A dermoscopic image of a skin lesion. A female patient, aged 28-32:
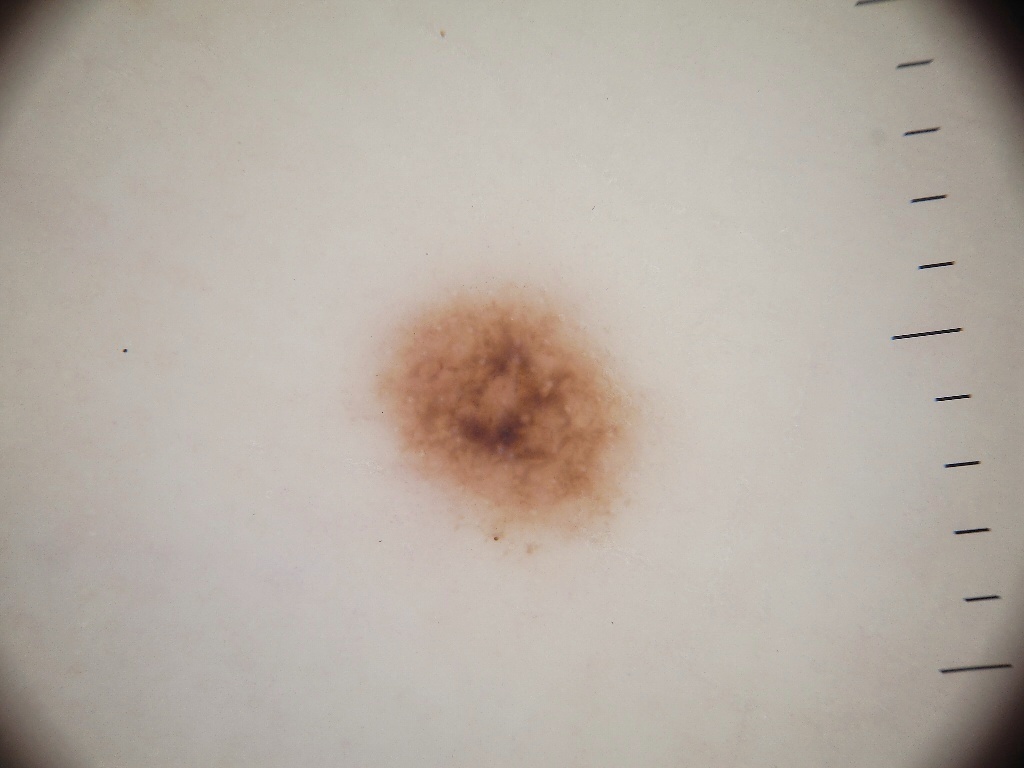Dermoscopic review identifies no pigment network, negative network, milia-like cysts, globules, or streaks. As (left, top, right, bottom), the lesion is located at [369,280,643,552]. Clinically diagnosed as a melanocytic nevus.